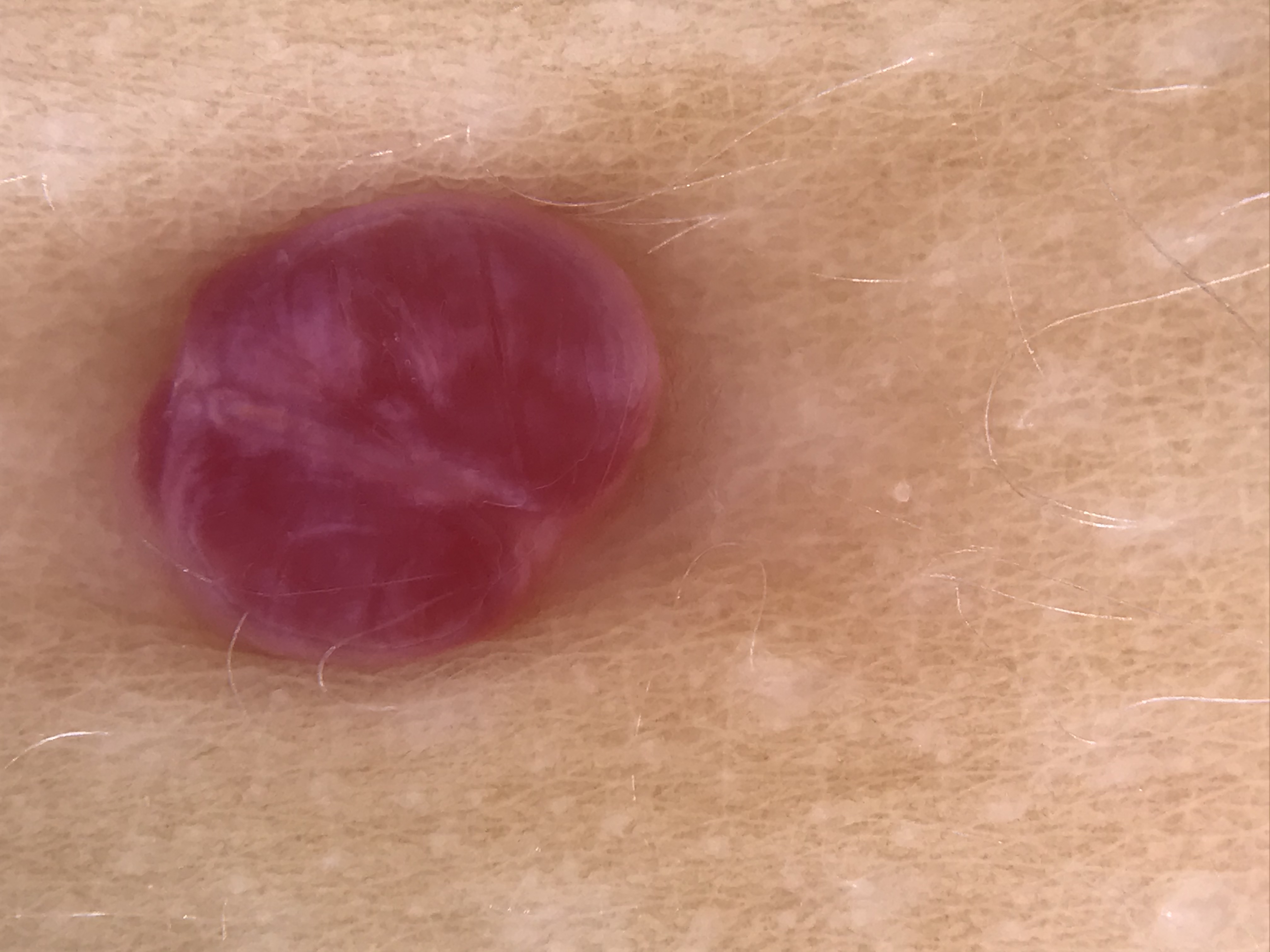assessment = pyogenic granuloma (expert consensus)